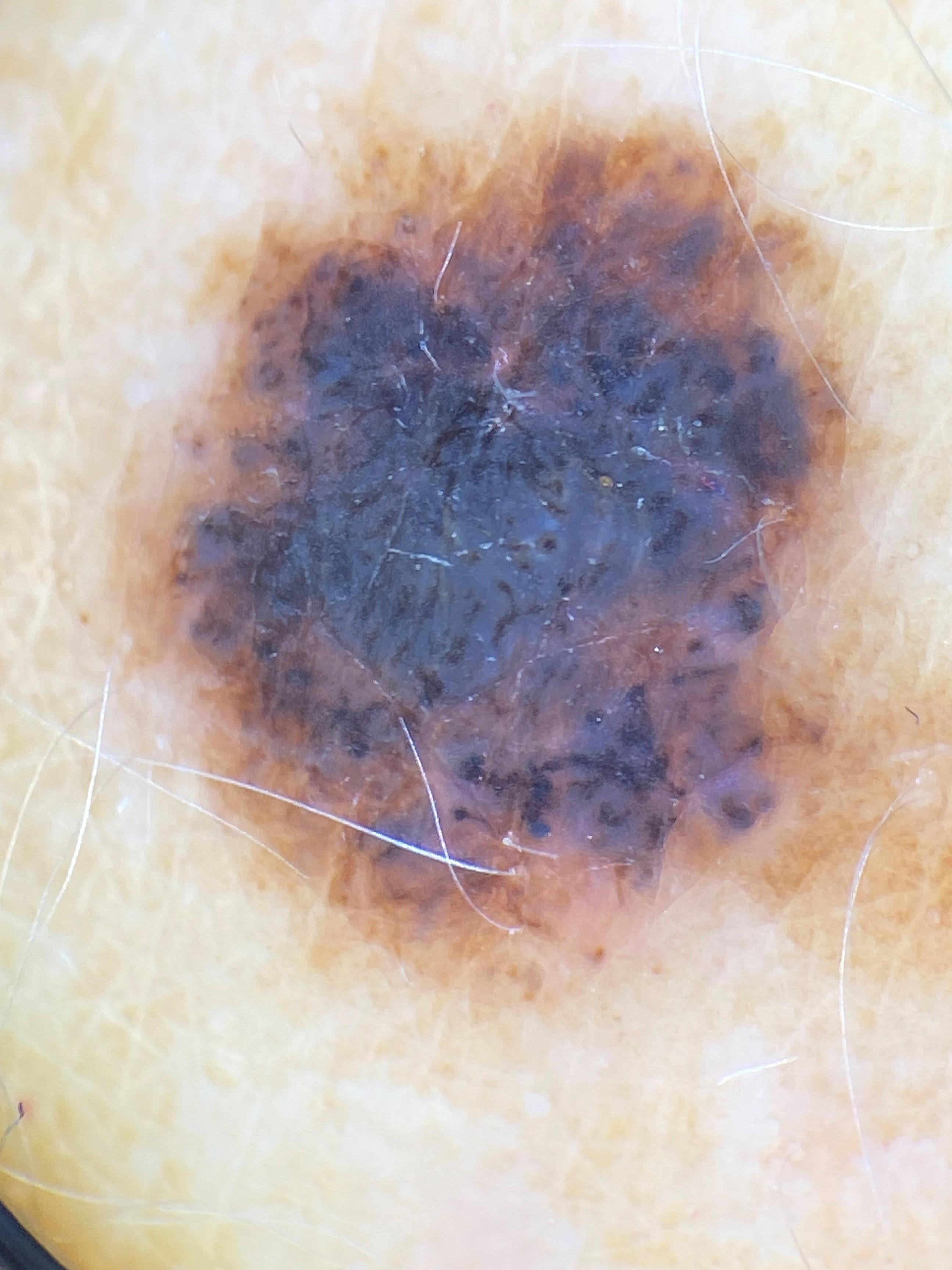subject = female, aged 43-47 | image = contact-polarized dermoscopy | skin type = II | anatomic site = a lower extremity | diagnostic label = Nevus (biopsy-proven).